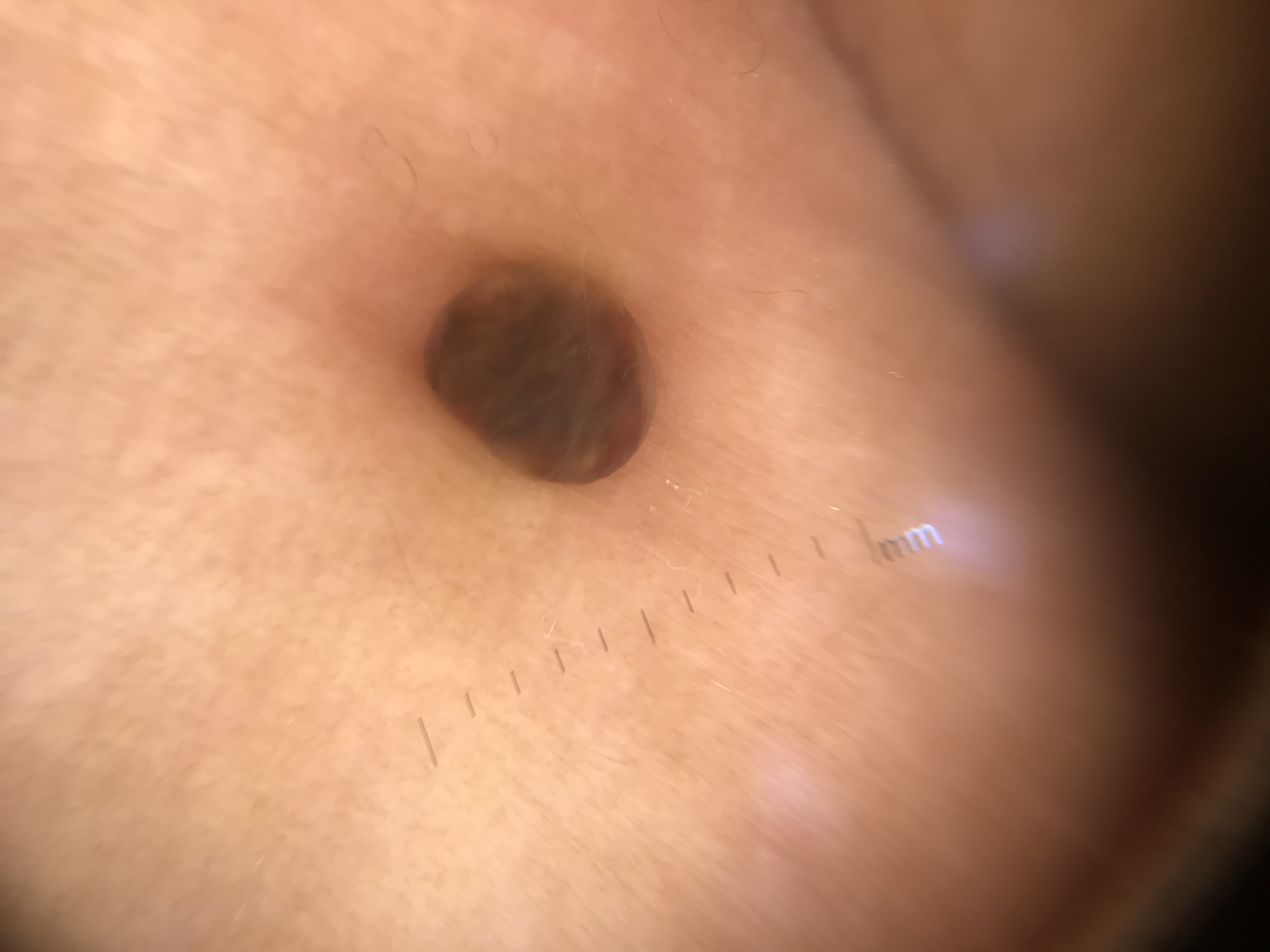The architecture is that of a banal lesion.
The diagnosis was a dermal nevus.